The patient described the issue as a rash; located on the palm, arm and back of the hand; the contributor reports enlargement, itching, pain, bleeding and burning; the condition has been present for more than one year; female subject, age 50–59; the photo was captured at a distance: 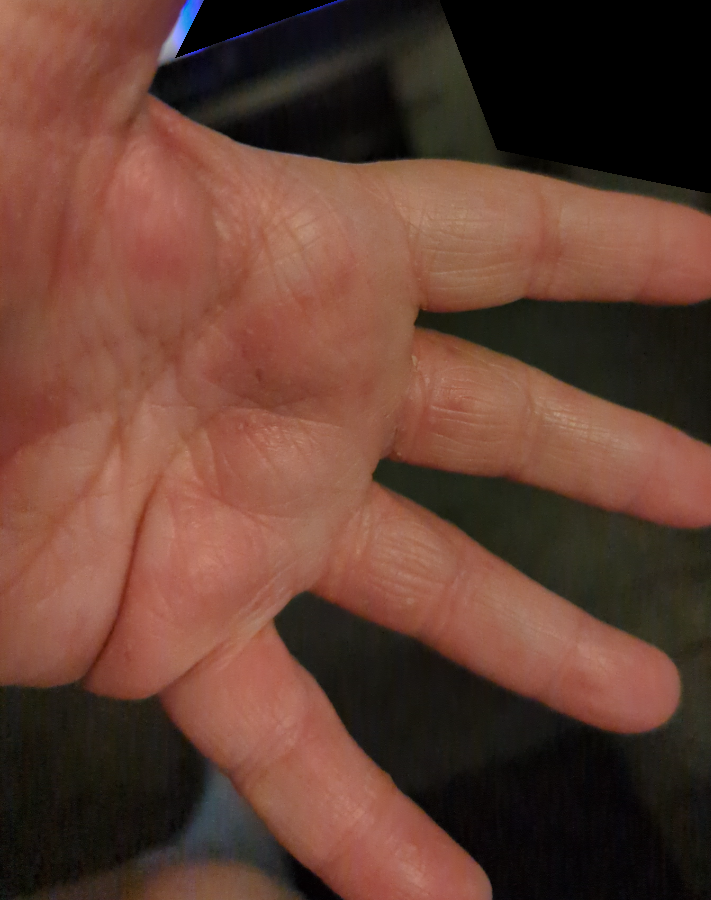differential diagnosis = reviewed remotely by one dermatologist: in keeping with Eczema